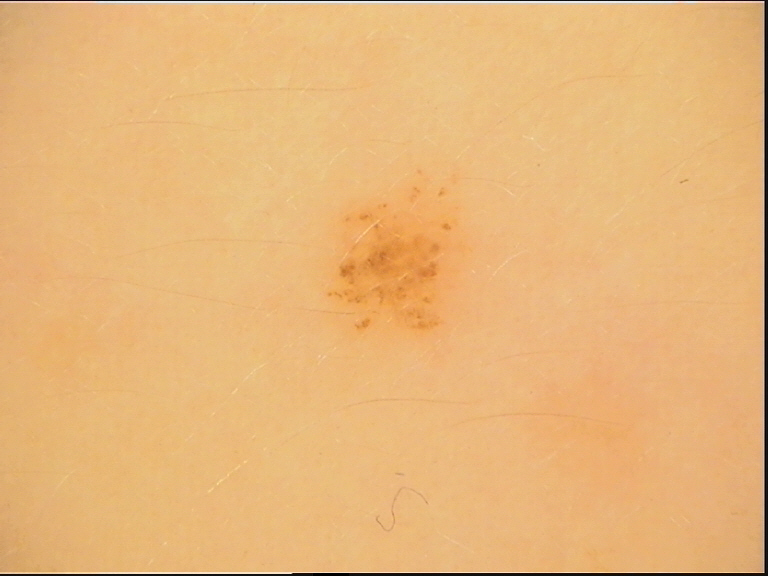Summary: A dermoscopic close-up of a skin lesion. Impression: Consistent with a dysplastic junctional nevus.